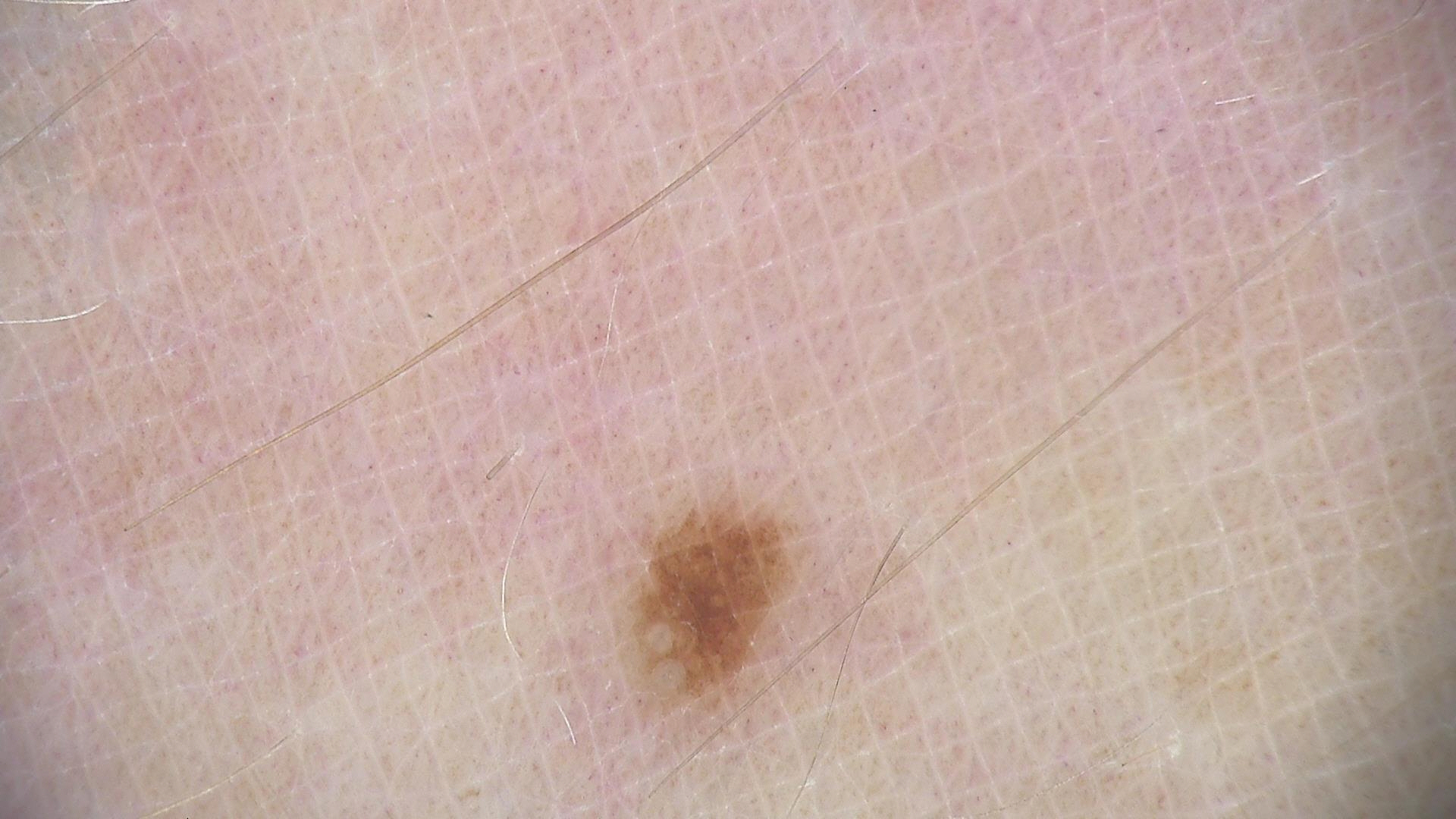Labeled as a banal lesion — a junctional nevus.